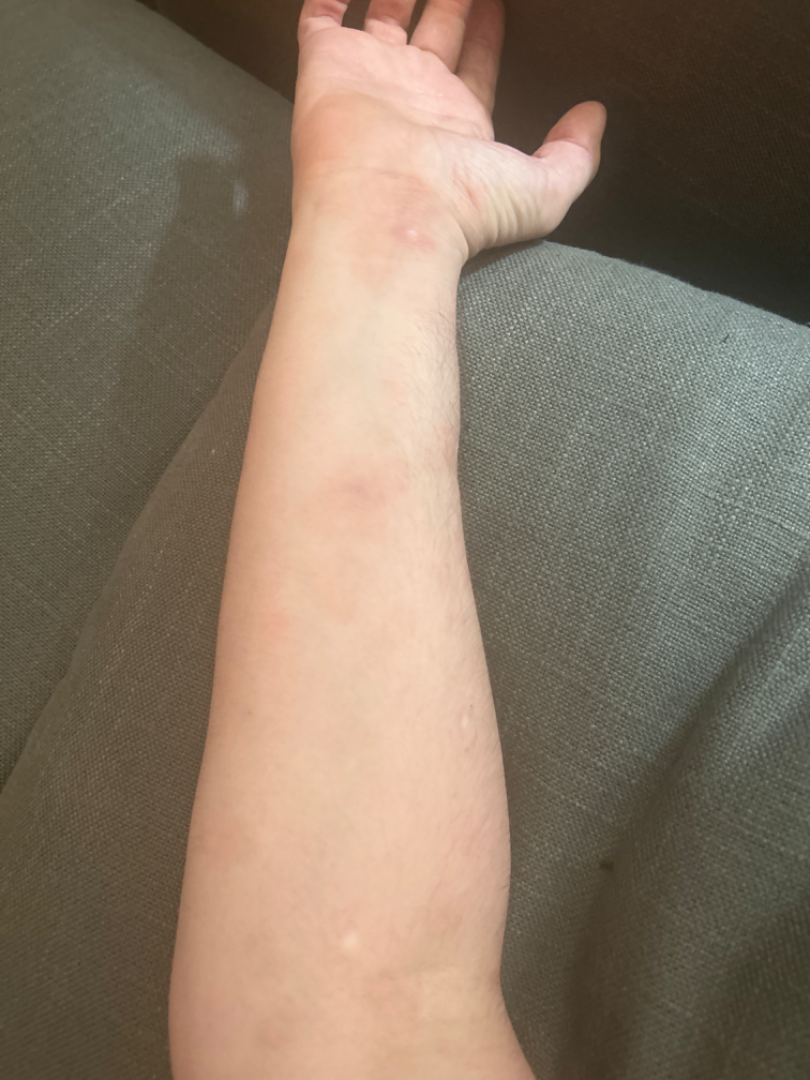The patient reported no relevant symptoms from the lesion. Reported duration is one to four weeks. The photograph was taken at a distance. The patient described the issue as a rash. The patient is 40–49, male. The arm, head or neck, front of the torso, back of the hand and back of the torso are involved.